A male subject 77 years of age; a moderate number of moles by the patient's own estimate; the patient says their skin reddens with sun exposure:
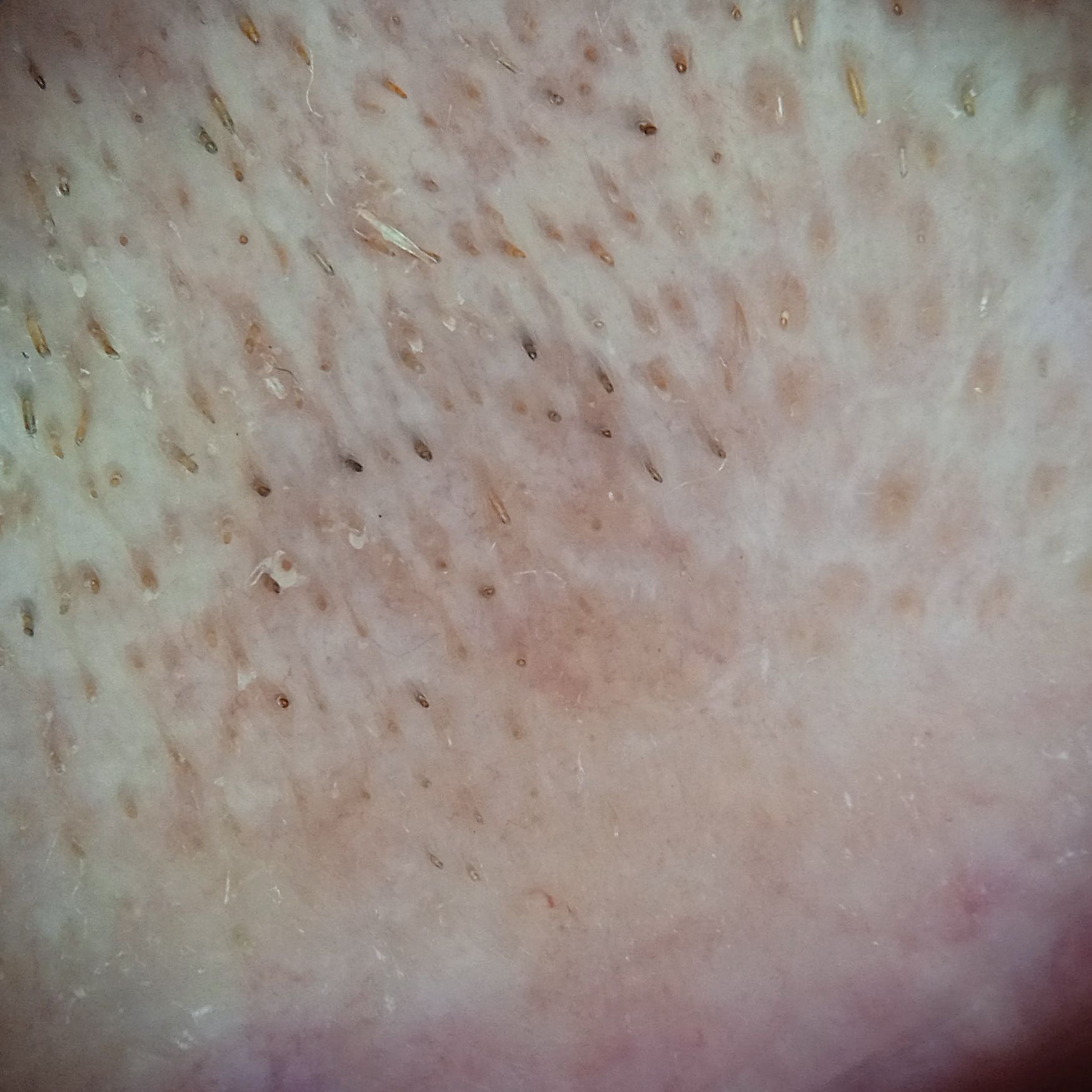The lesion is located on the face.
Measuring roughly 6.4 mm.
Dermatologist review favored an actinic keratosis.